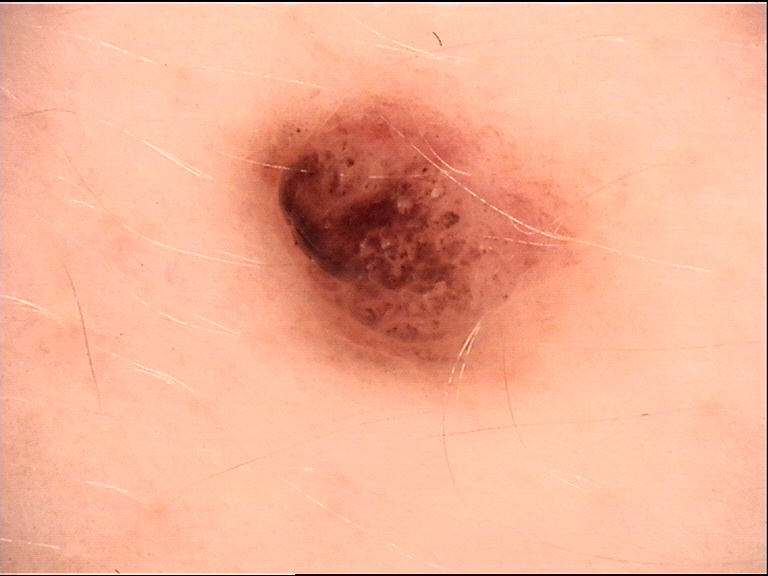Findings:
A dermoscopic photograph of a skin lesion.
Impression:
Classified as a banal lesion — a compound nevus.